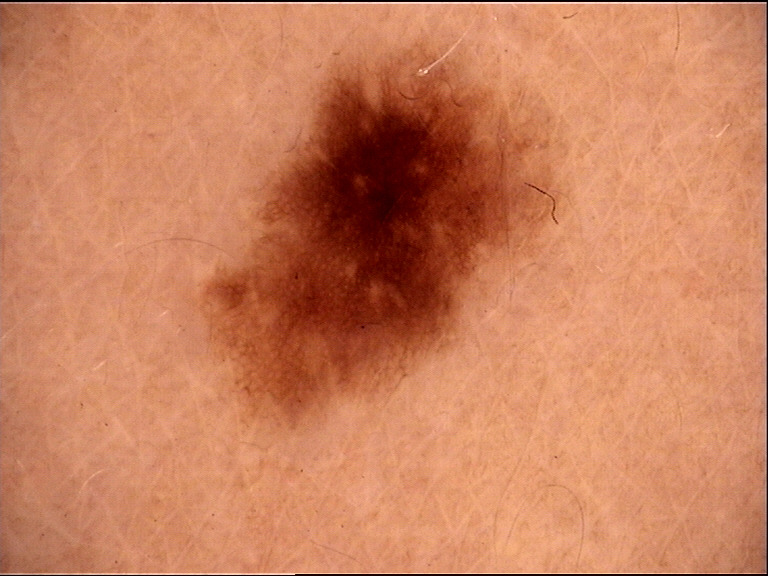The diagnosis was a dysplastic junctional nevus.